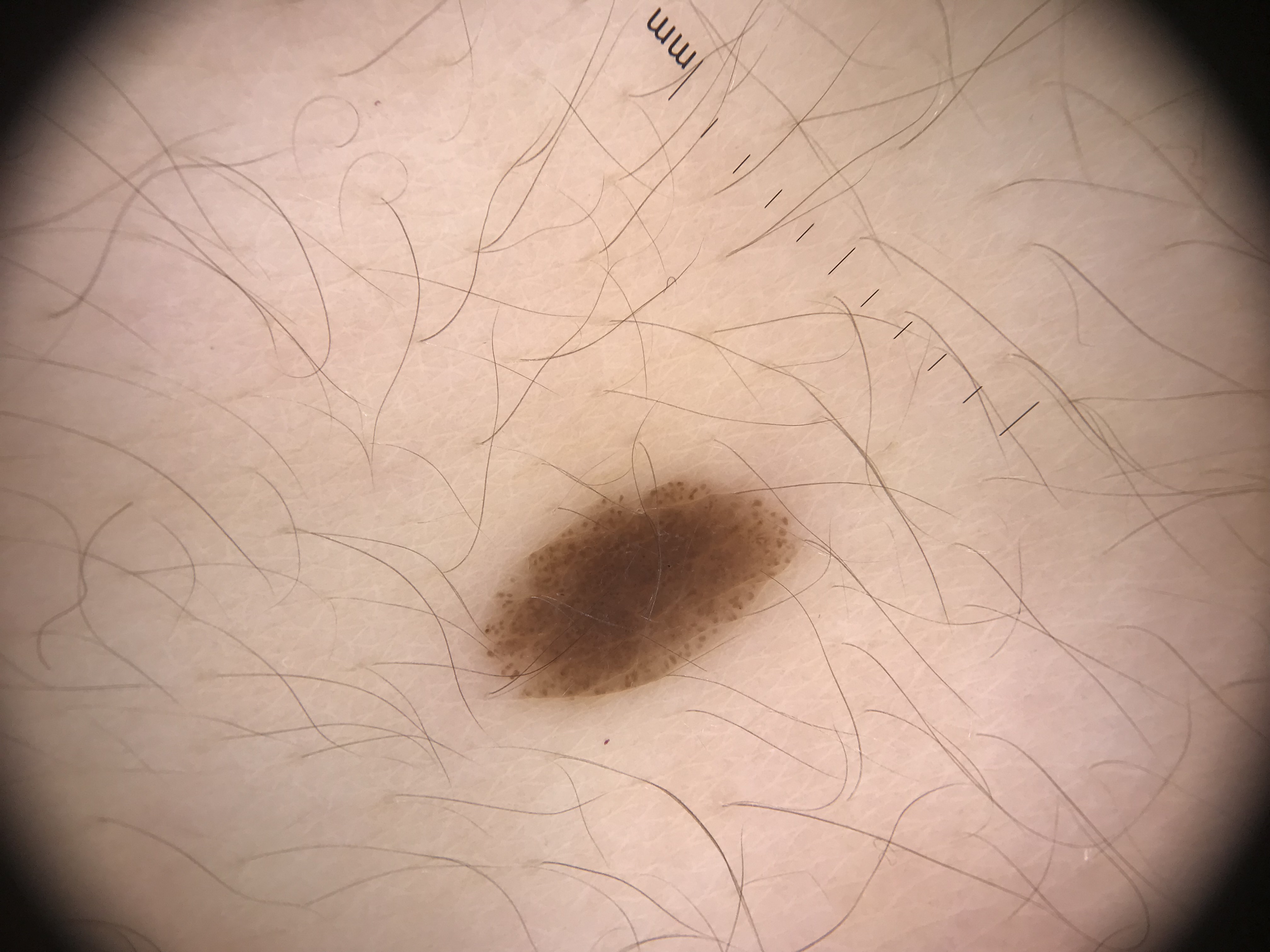modality: dermatoscopy; diagnostic label: junctional nevus (expert consensus).